The subject is 60–69, female · the photograph is a close-up of the affected area · the arm and front of the torso are involved.
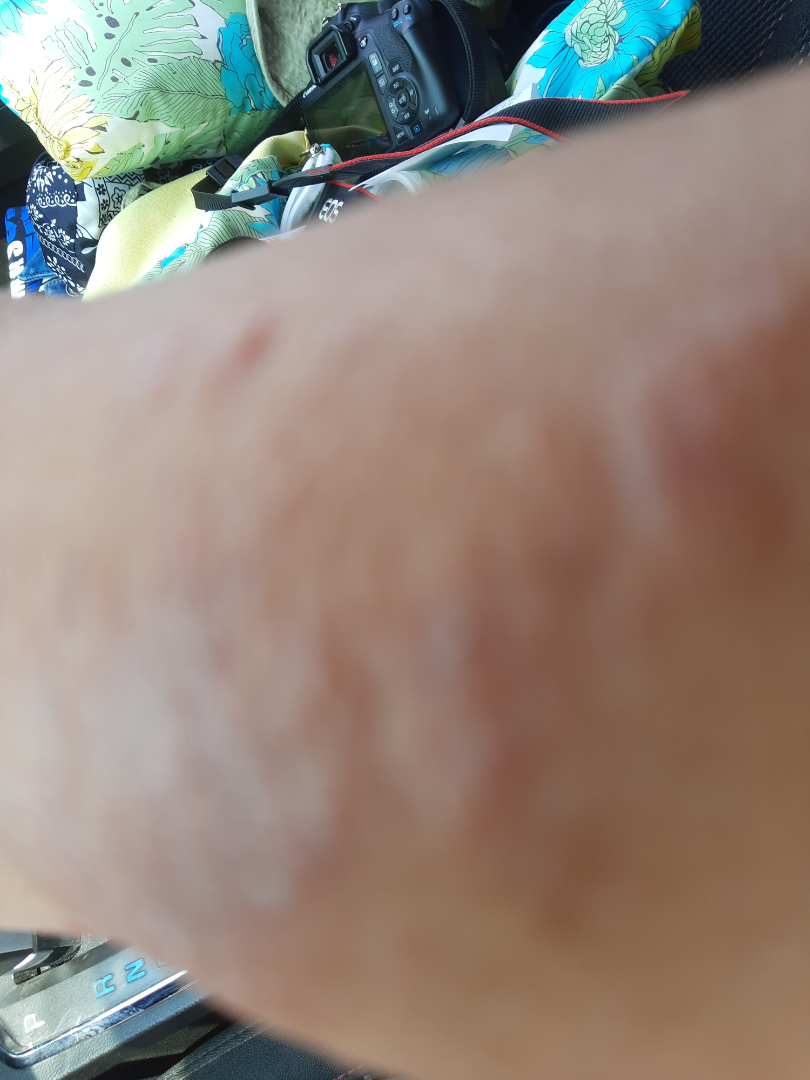Associated systemic symptoms include joint pain and fatigue. The patient described the issue as skin that appeared healthy to them. Symptoms reported: itching, burning and enlargement. The lesion is described as rough or flaky and raised or bumpy. Reviewed remotely by one dermatologist: consistent with Chronic dermatitis, NOS.